A female subject in their mid- to late 50s, a dermoscopy image of a single skin lesion.
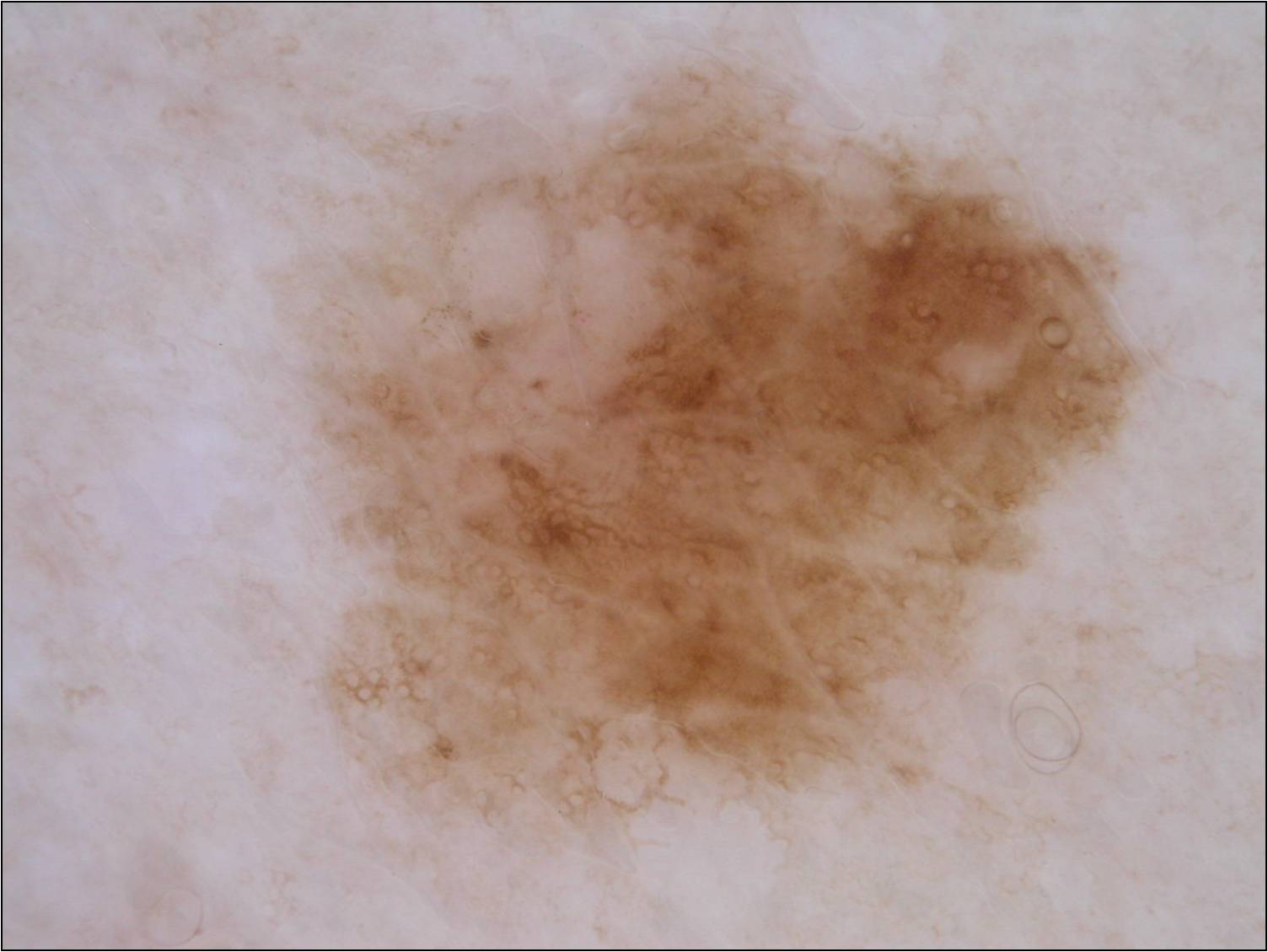Image and clinical context: In (x1, y1, x2, y2) order, the visible lesion spans <bbox>305, 57, 1159, 845</bbox>. The dermoscopic pattern shows pigment network. Conclusion: Histopathology confirmed a melanoma.